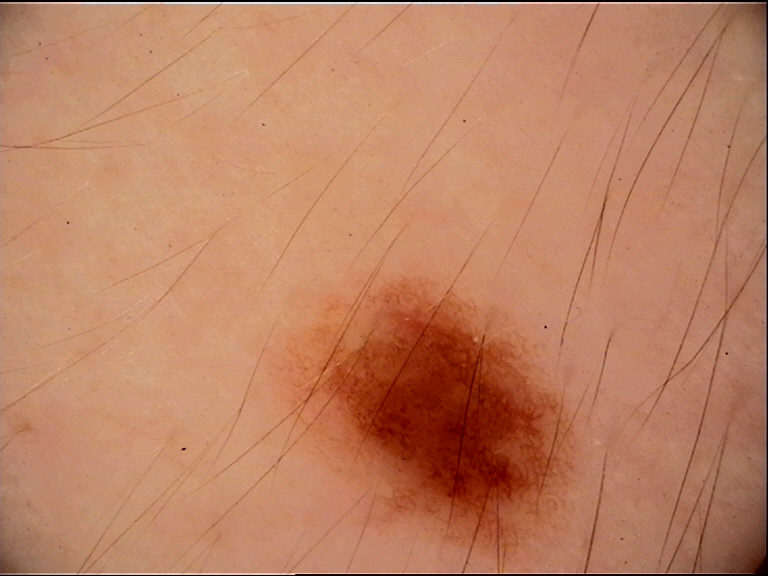Classified as a dysplastic junctional nevus.